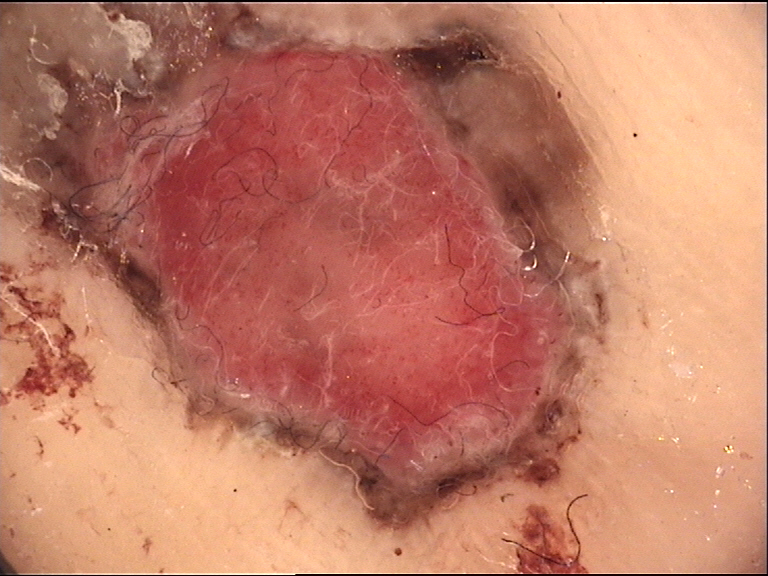Confirmed on histopathology as an acral nodular melanoma.